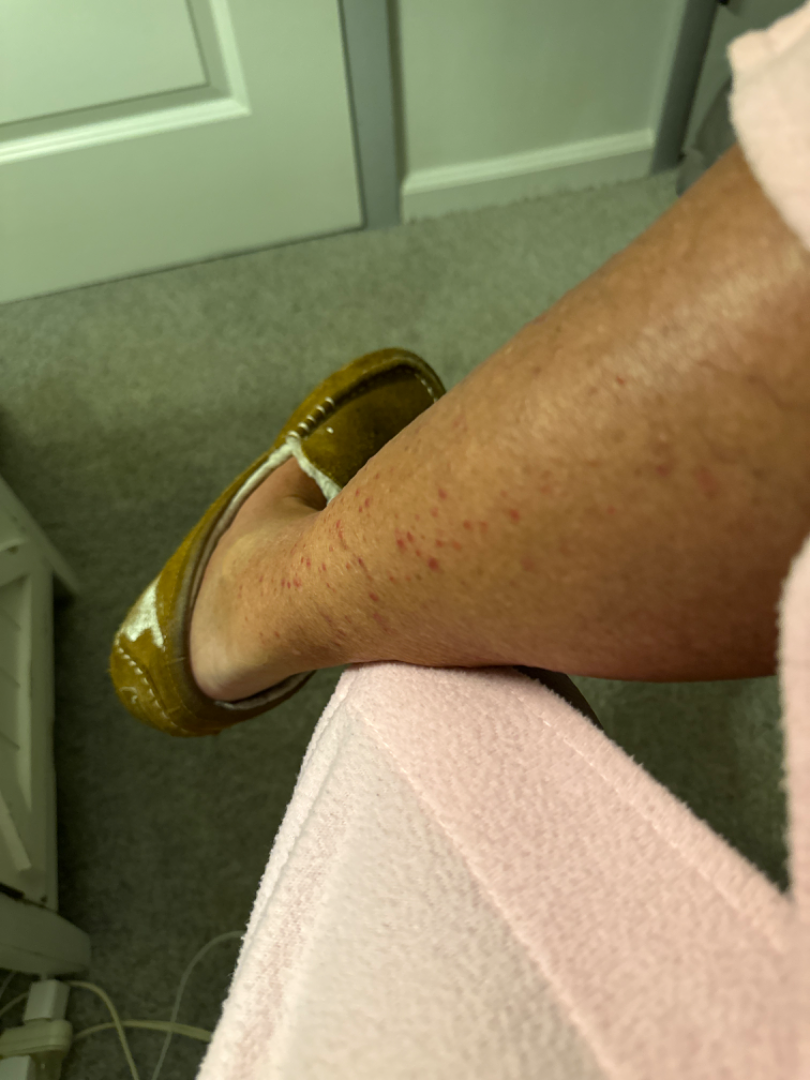<case>
  <shot_type>at a distance</shot_type>
  <duration>less than one week</duration>
  <body_site>leg, arm</body_site>
  <texture>raised or bumpy</texture>
  <patient>female, age 50–59</patient>
  <differential>
    <leading>Hypersensitivity</leading>
    <considered>Lichen planus/lichenoid eruption</considered>
  </differential>
</case>